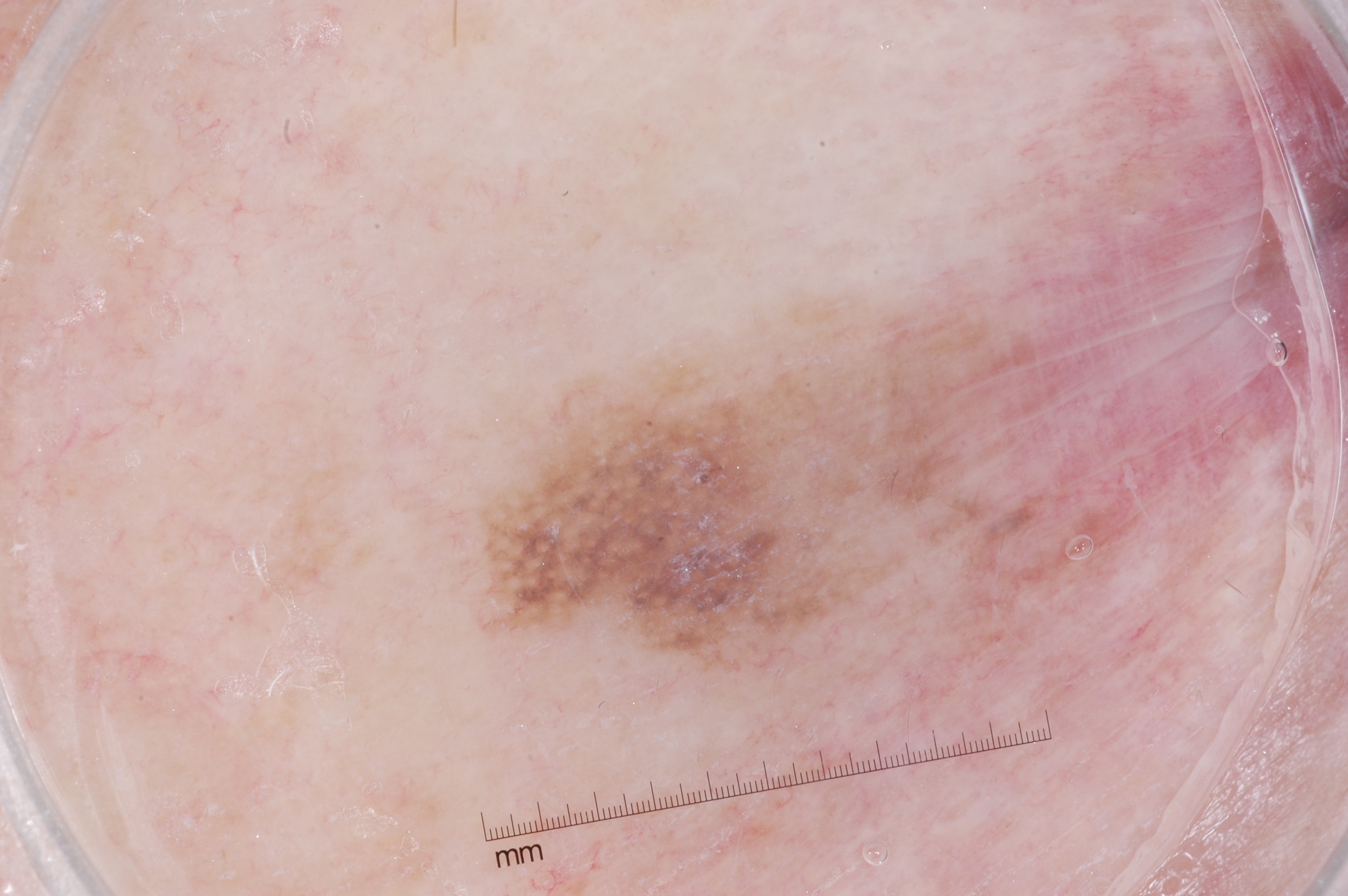A dermoscopic view of a skin lesion.
The subject is a female aged 48-52.
The dermoscopic pattern shows no pigment network, negative network, streaks, or milia-like cysts.
The lesion occupies roughly 11% of the field.
As (left, top, right, bottom), the lesion is bounded by box(465, 299, 1007, 671).
Confirmed on histopathology as a melanoma.